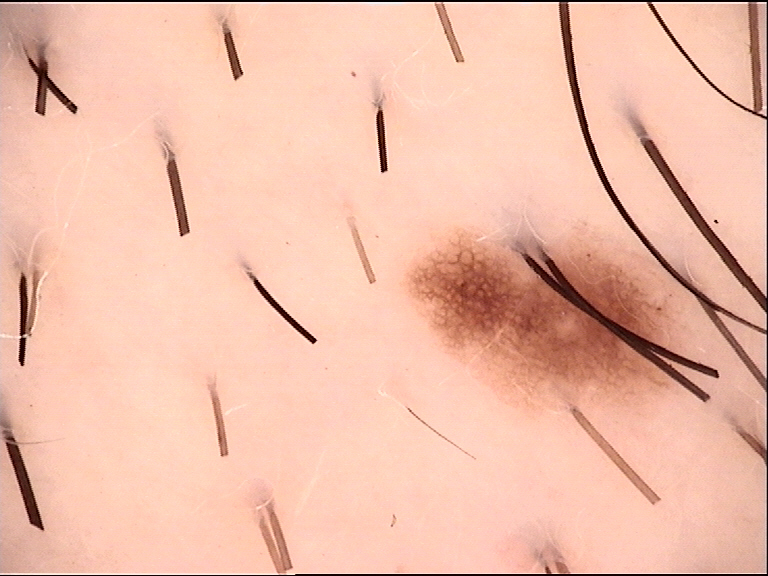A dermatoscopic image of a skin lesion.
Consistent with a dysplastic junctional nevus.